The patient says their skin reddens painfully with sun exposure; a female subject 50 years of age; the referring clinician suspected melanoma.
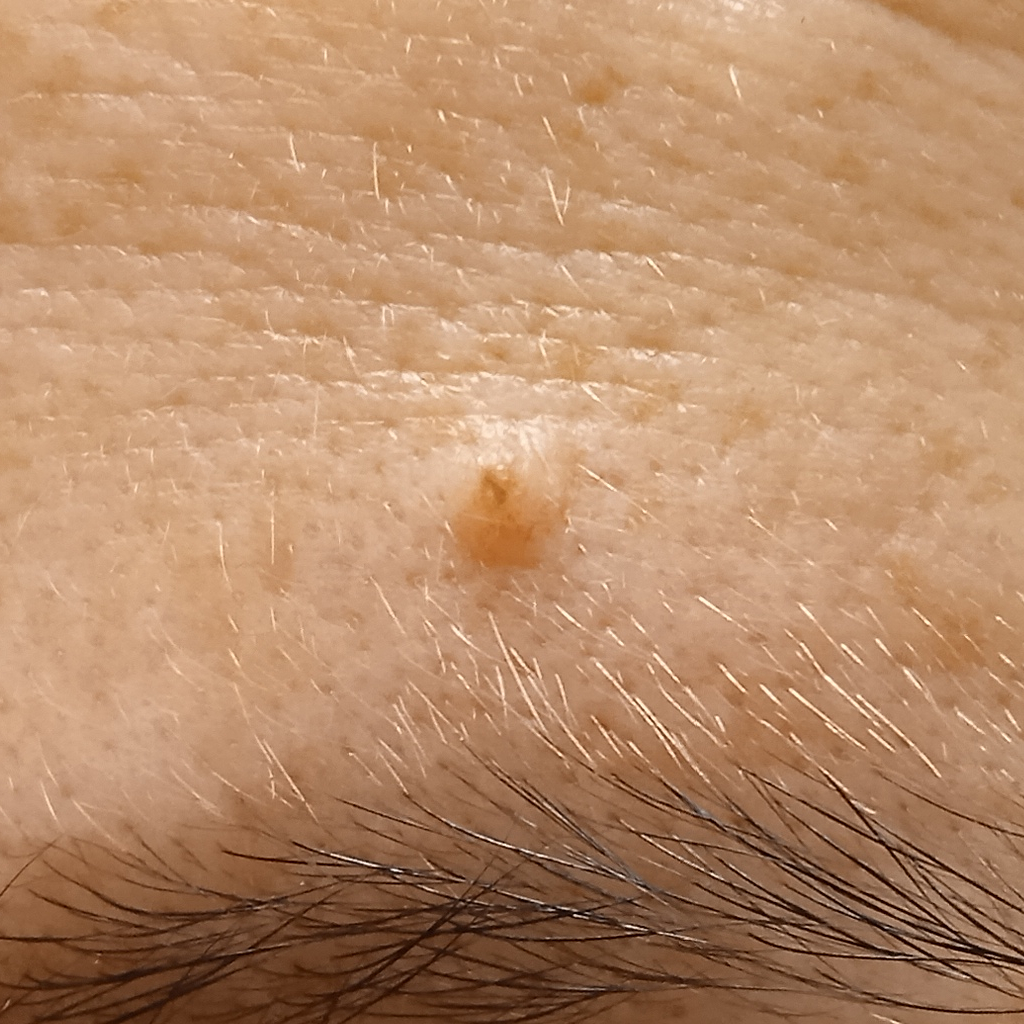The dermatologists' assessment was a melanocytic nevus.